An image taken at a distance; the palm, leg and arm are involved; the patient is 18–29, female: 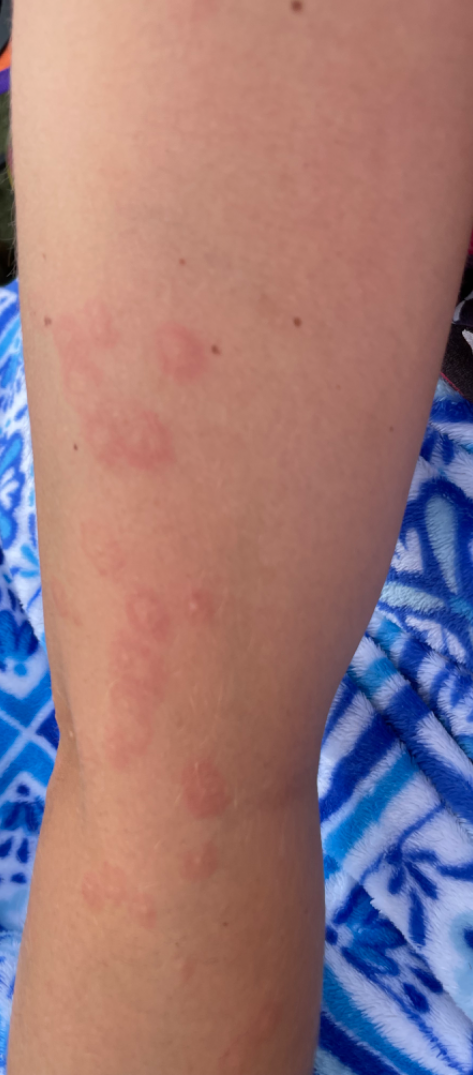{
  "texture": [
    "raised or bumpy",
    "fluid-filled"
  ],
  "differential": {
    "leading": [
      "Erythema multiforme"
    ],
    "considered": [
      "Drug Rash"
    ]
  }
}